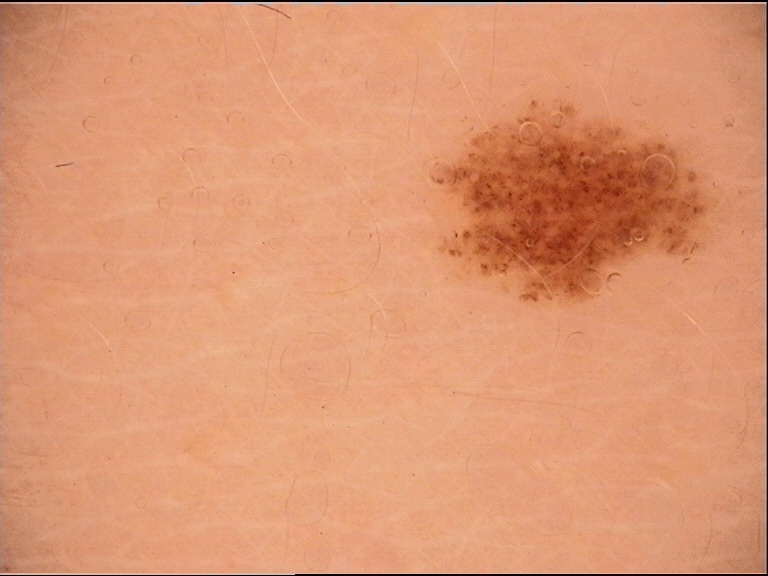Consistent with a banal lesion — a junctional nevus.